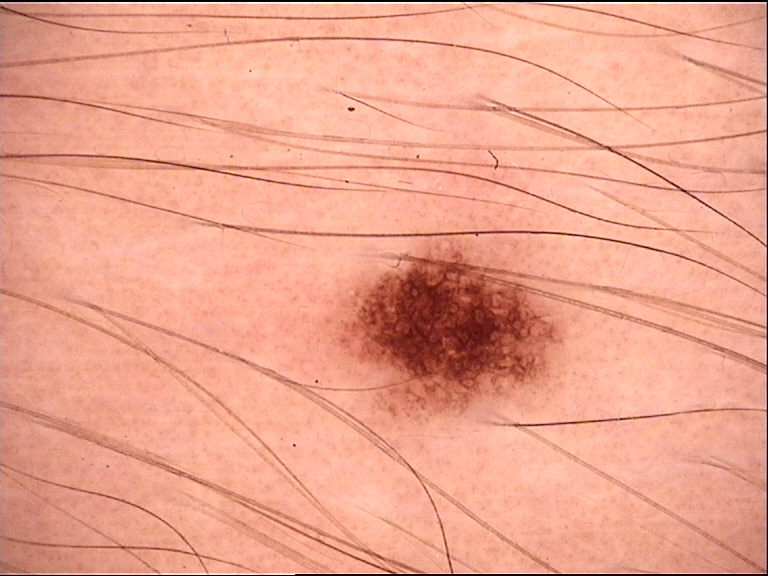The morphology is that of a banal lesion. The diagnostic label was a junctional nevus.